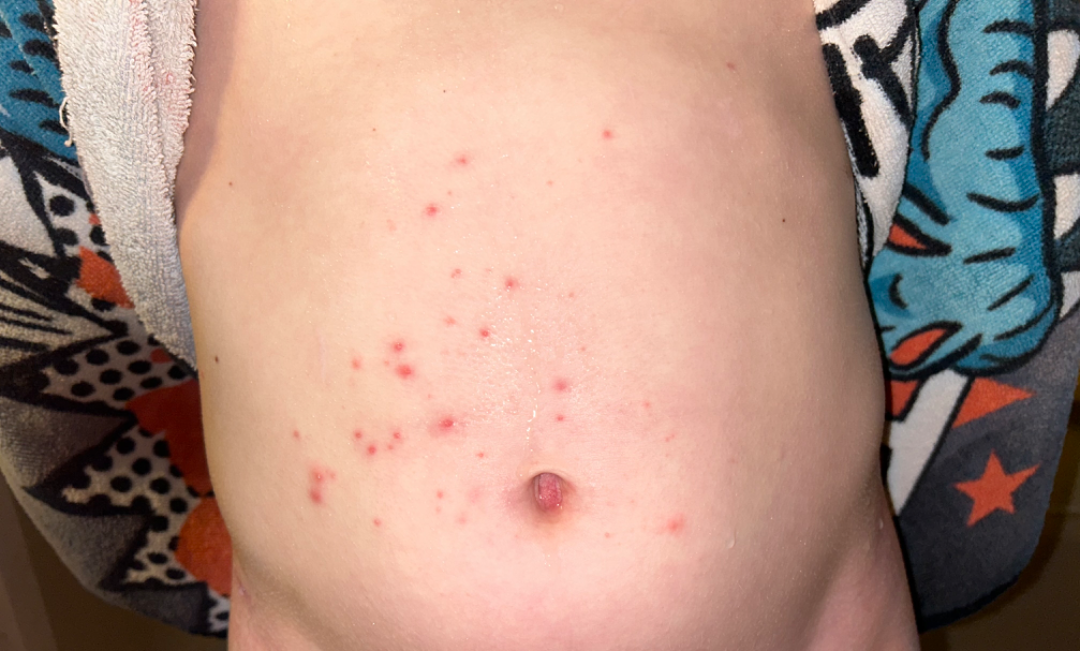Assessment: Single-reviewer assessment: most consistent with Chicken pox exanthem.